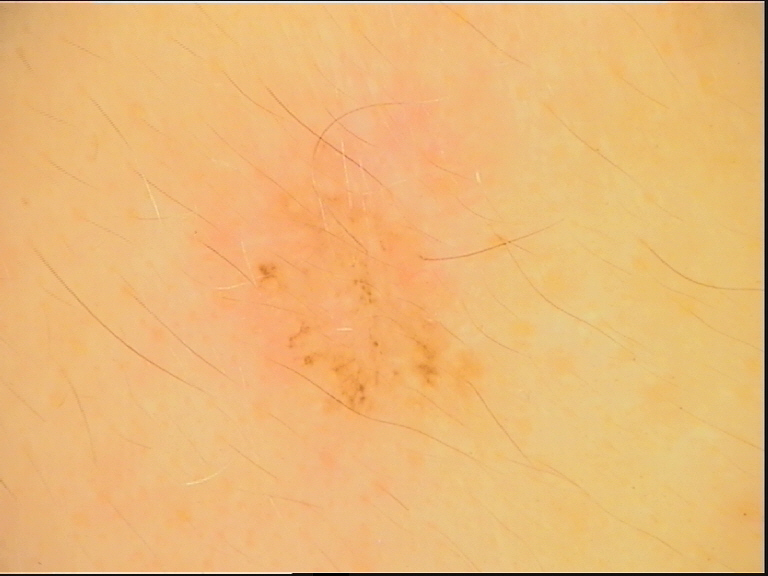A dermoscopic close-up of a skin lesion. Classified as a dysplastic junctional nevus.